A female subject in their late 70s · a clinical close-up photograph of a skin lesion:
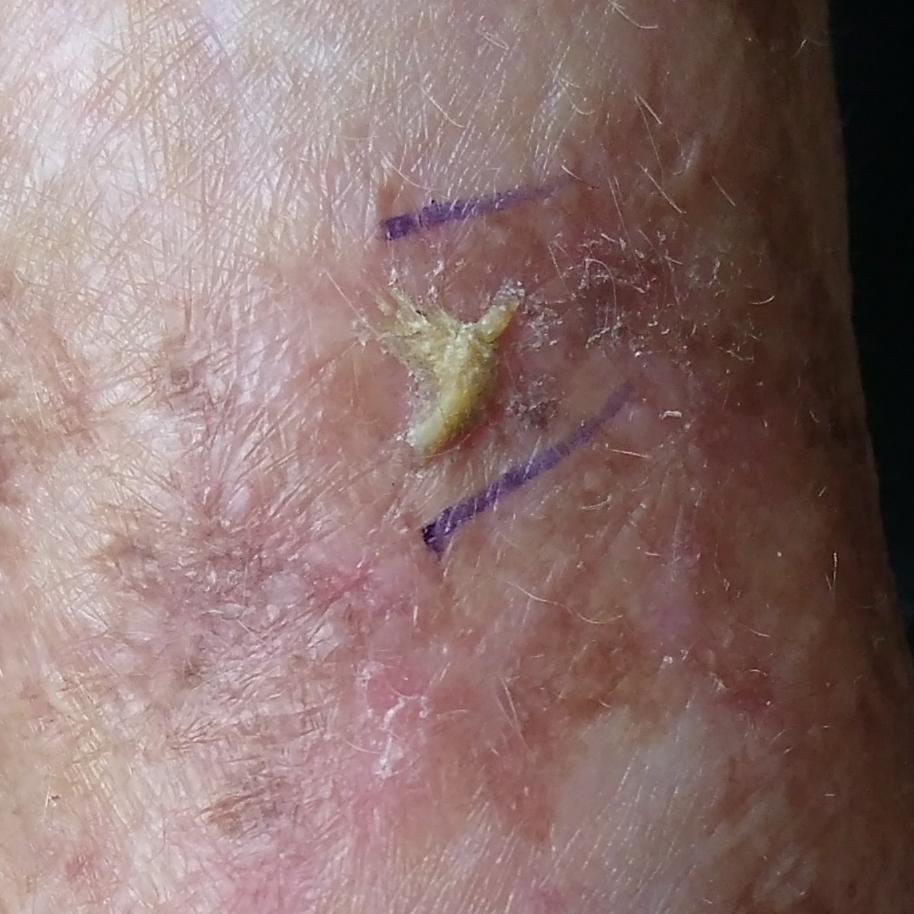Findings:
The lesion is on a hand. Per patient report, the lesion has grown, itches, and is elevated.
Conclusion:
The diagnostic impression was a premalignant lesion — an actinic keratosis.